Located on the top or side of the foot, head or neck and leg · an image taken at a distance · the lesion is described as raised or bumpy and fluid-filled:
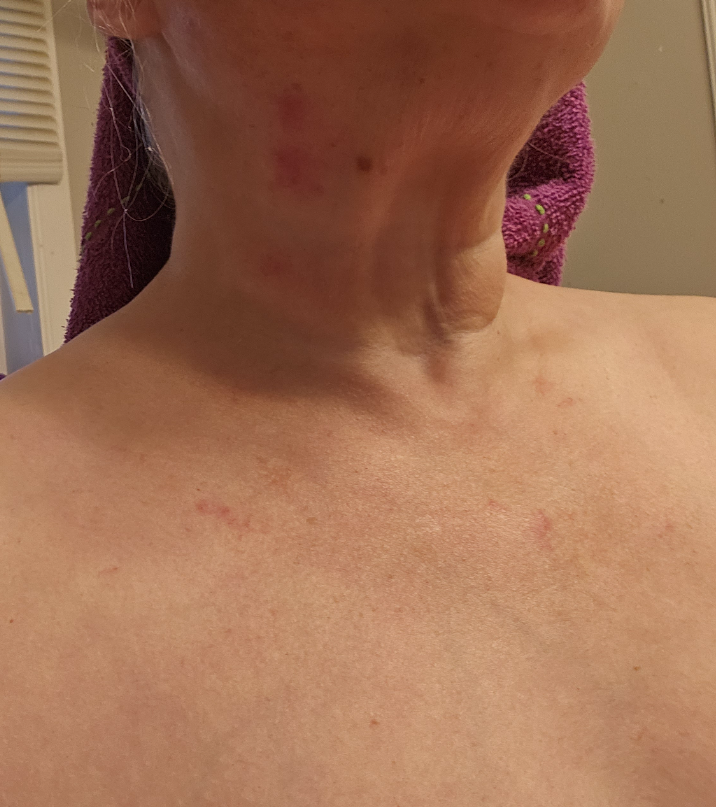differential: Allergic Contact Dermatitis (considered); Irritant Contact Dermatitis (considered)